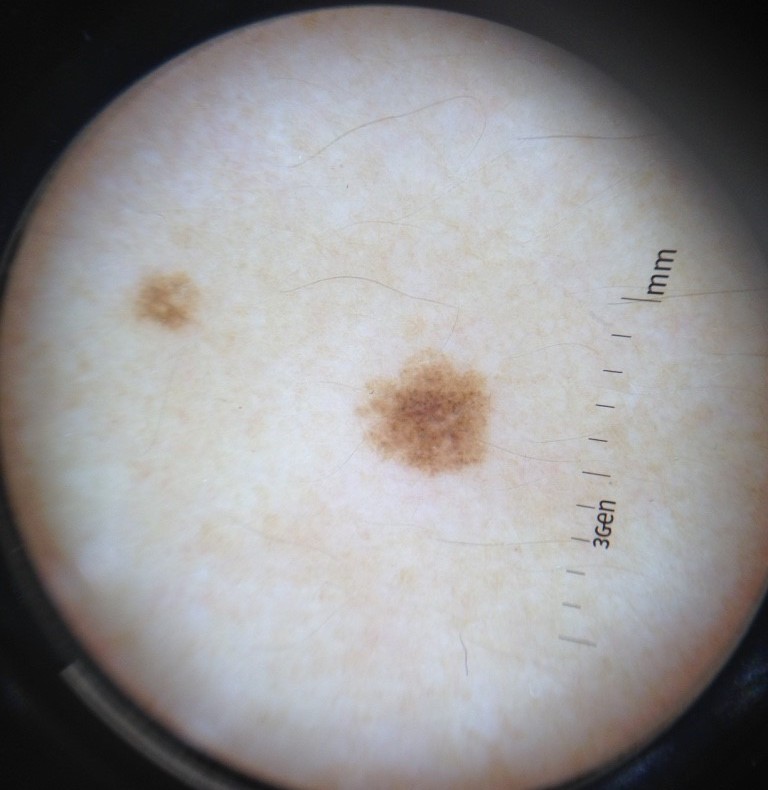– image — dermatoscopy
– diagnosis — dysplastic junctional nevus (expert consensus)